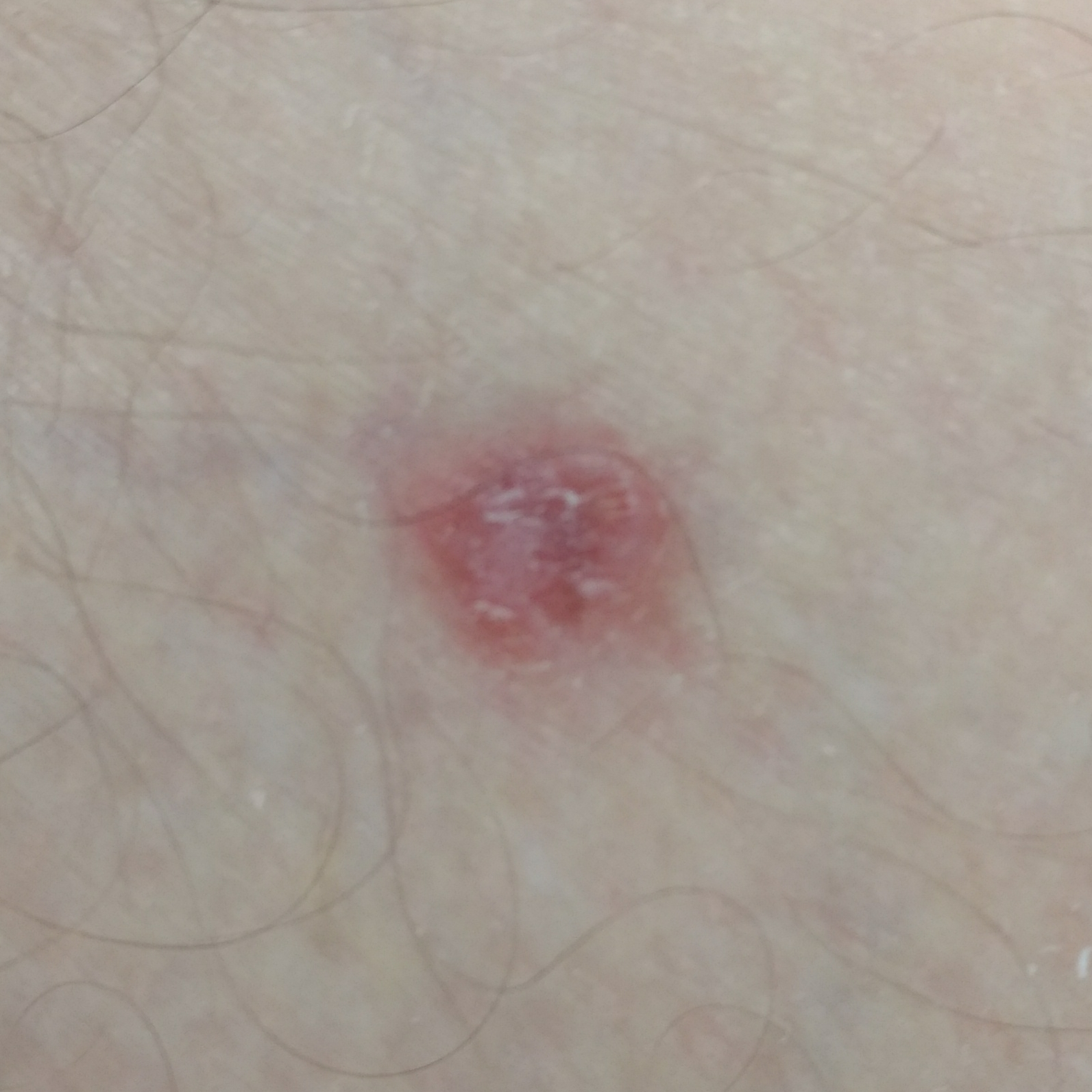patient = male, 85 years old; site = a thigh; symptoms = elevation, change in appearance, growth; diagnostic label = basal cell carcinoma (biopsy-proven).